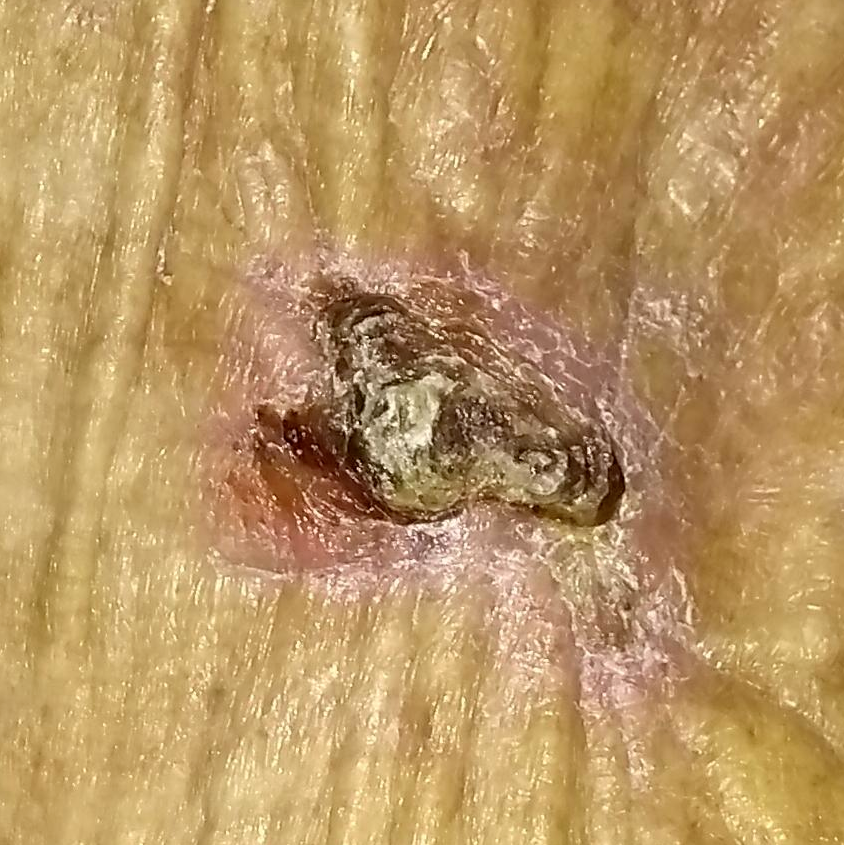| field | value |
|---|---|
| skin type | II |
| patient-reported symptoms | growth, elevation, pain, itching, bleeding / no change in appearance |
| pathology | basal cell carcinoma (biopsy-proven) |